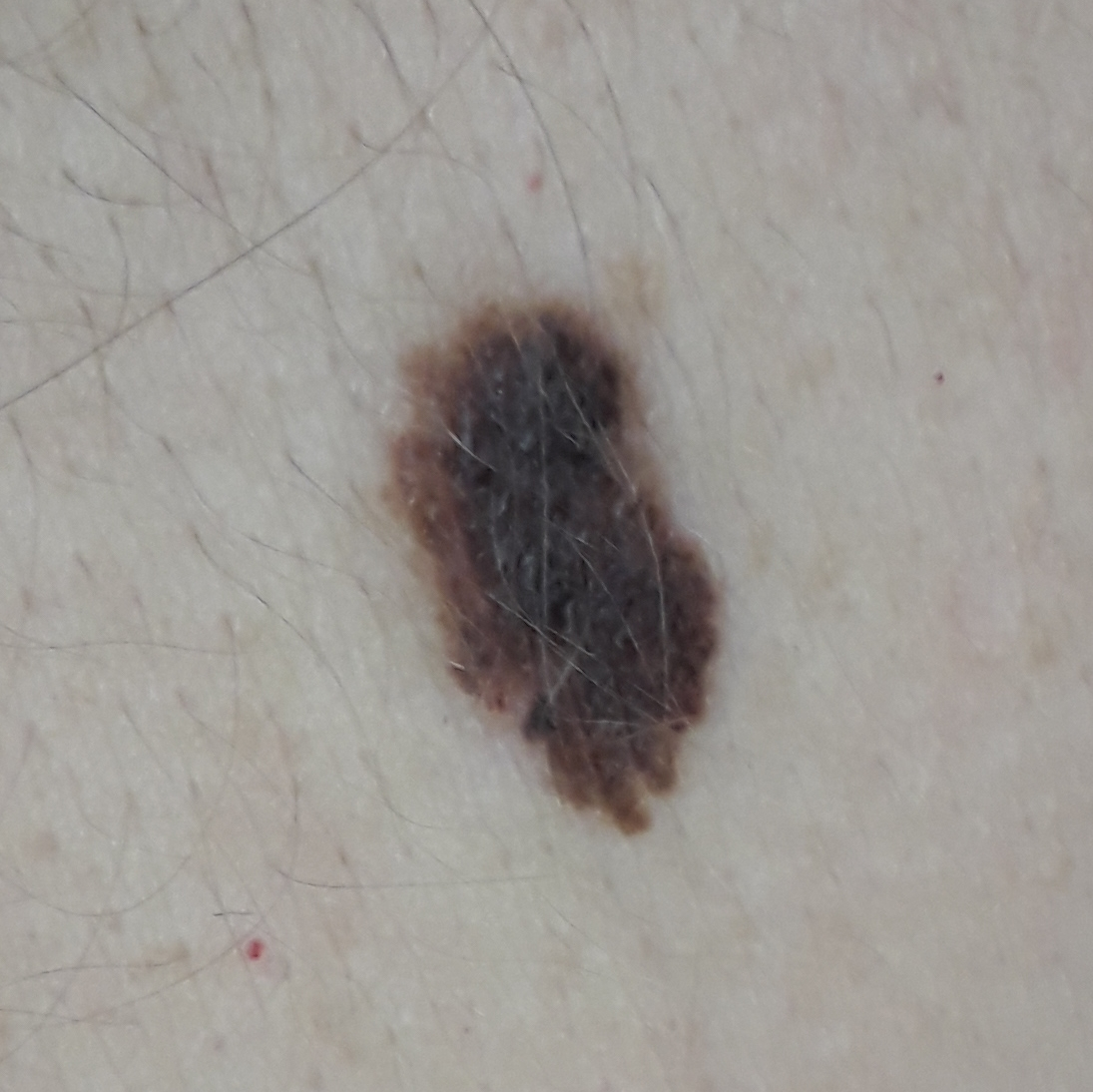Case summary: By history, prior malignancy (patient or family). The patient is Fitzpatrick phototype IV. A female patient 43 years of age. A smartphone photograph of a skin lesion. The lesion involves the neck. The lesion measures 20 × 8 mm. Per patient report, the lesion has grown. Conclusion: Histopathological examination showed a melanoma.